A dermoscopy image of a single skin lesion.
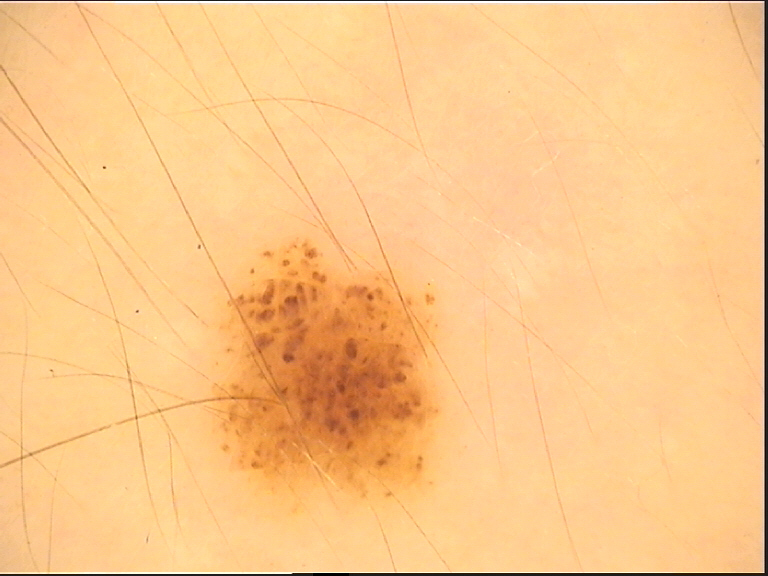The diagnostic label was a benign lesion — a dysplastic junctional nevus.